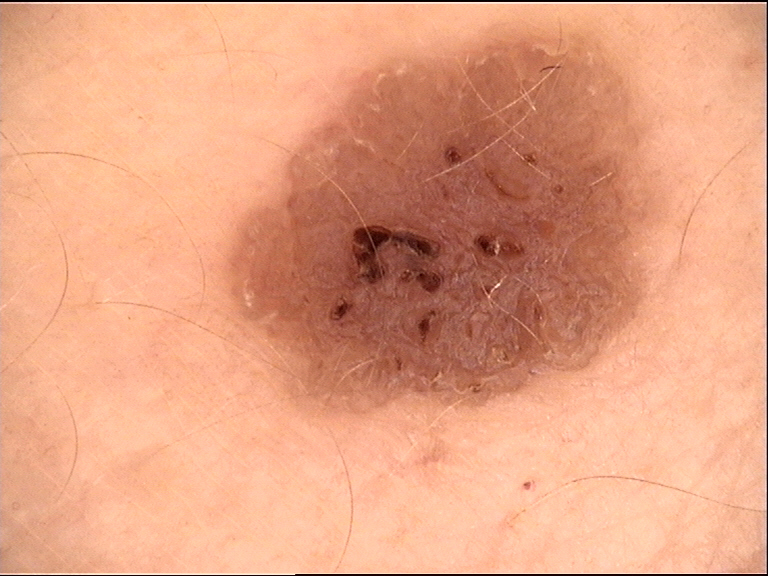Findings:
A dermoscopy image of a single skin lesion. The architecture is that of a keratinocytic lesion.
Conclusion:
The diagnosis was a seborrheic keratosis.